Collected as part of a research study, without a referral diagnosis:
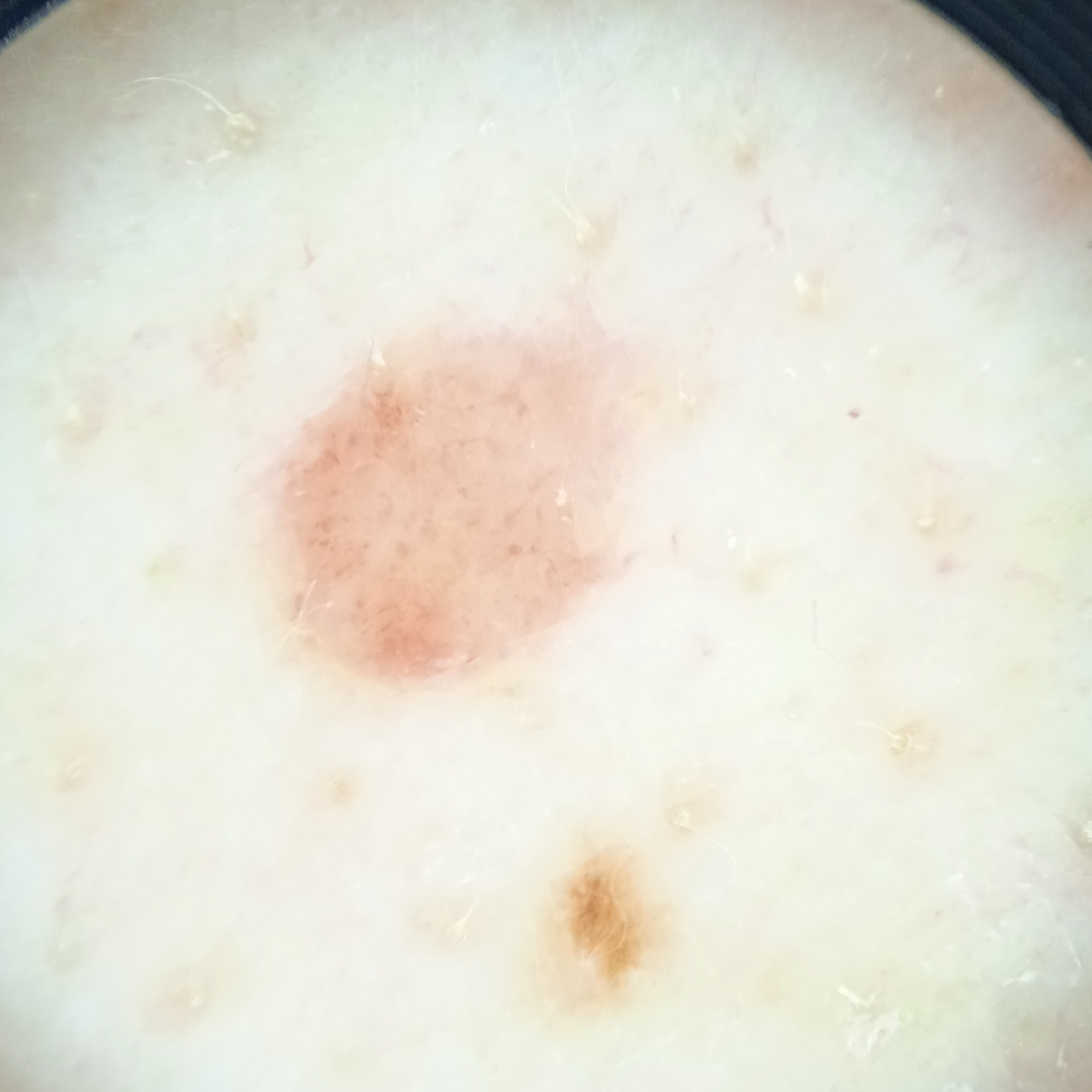site = the back, size = 4.4 mm, assessment = melanocytic nevus (dermatologist consensus).